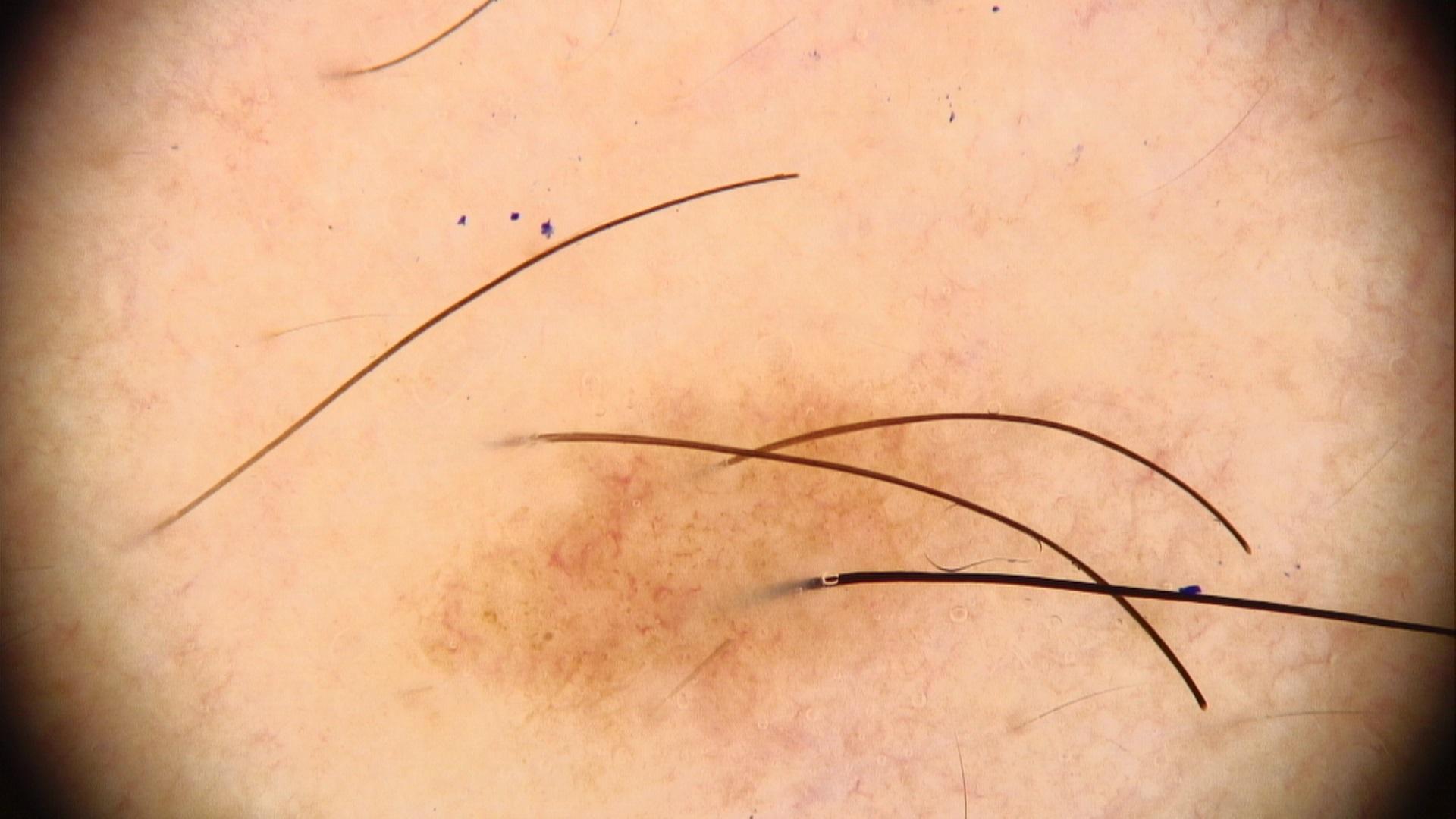A male patient aged around 20.
The lesion involves a lower extremity.
Clinically diagnosed as a nevus.